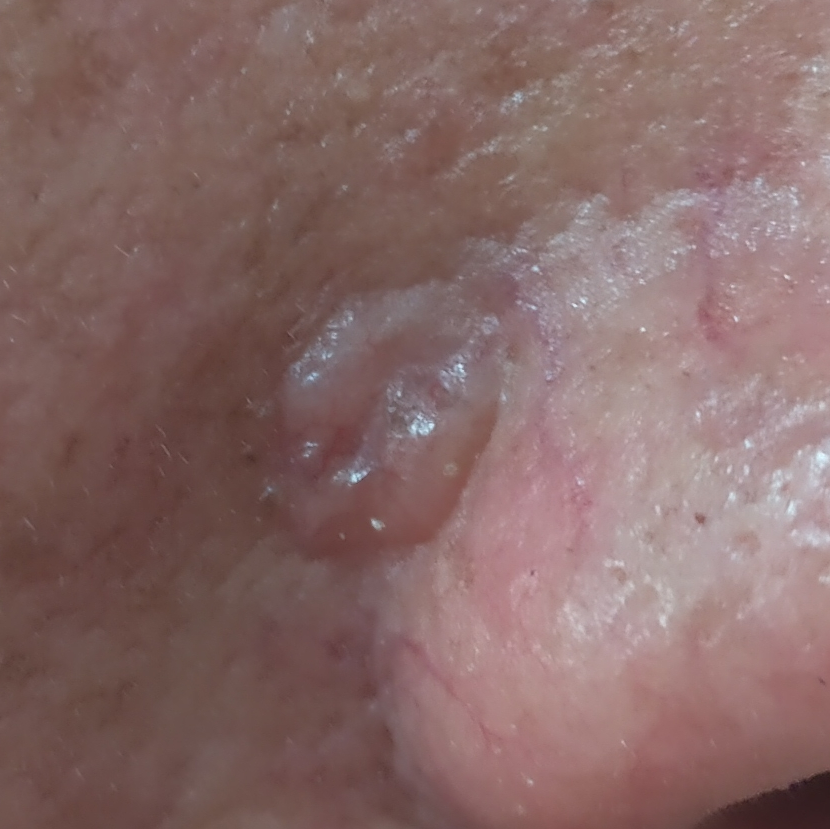By history, alcohol use, prior skin cancer (patient or family), pesticide exposure, and no prior malignancy (patient or family).
A clinical close-up photograph of a skin lesion.
A male patient age 51.
By the patient's account, the lesion is elevated.
The biopsy diagnosis was a basal cell carcinoma.